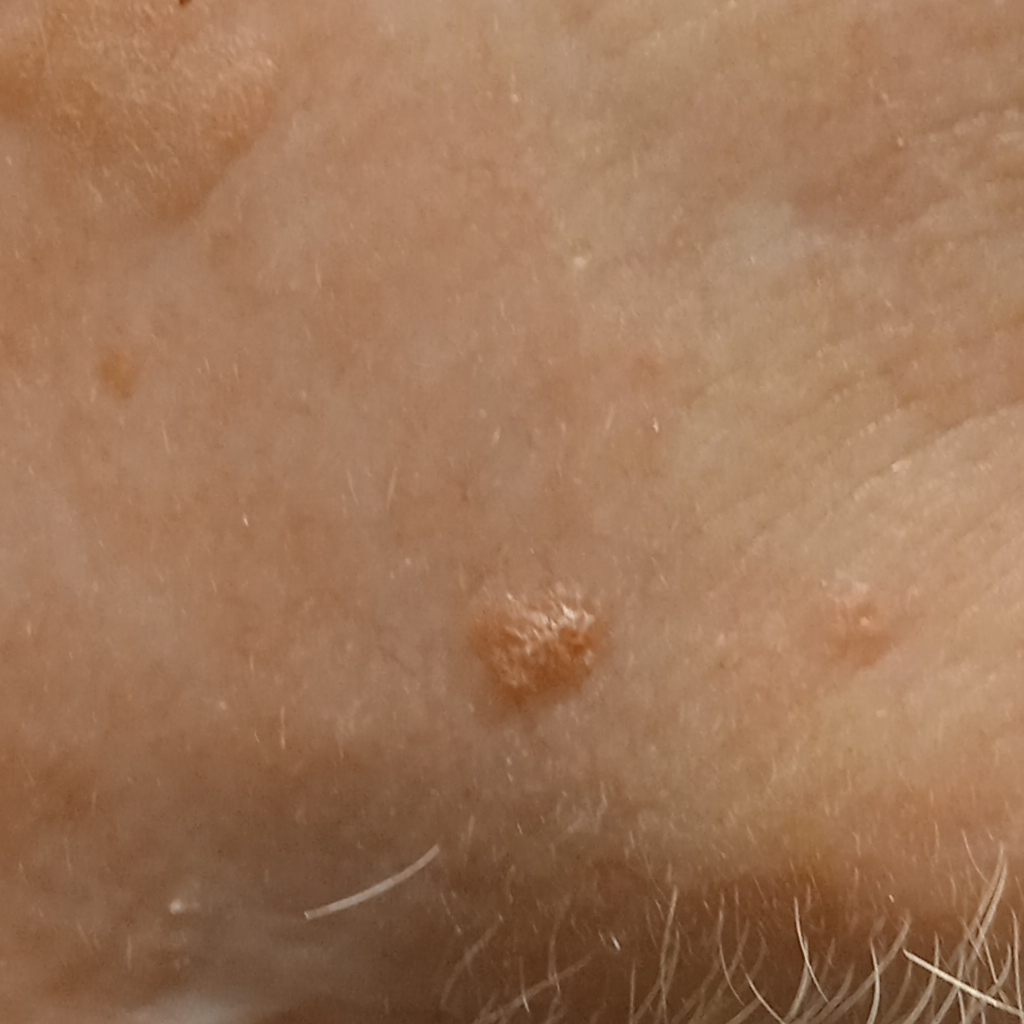Findings:
- referral: research study (no referral diagnosis)
- patient: male, aged 77
- size: 4.3 mm
- assessment: actinic keratosis (dermatologist consensus)